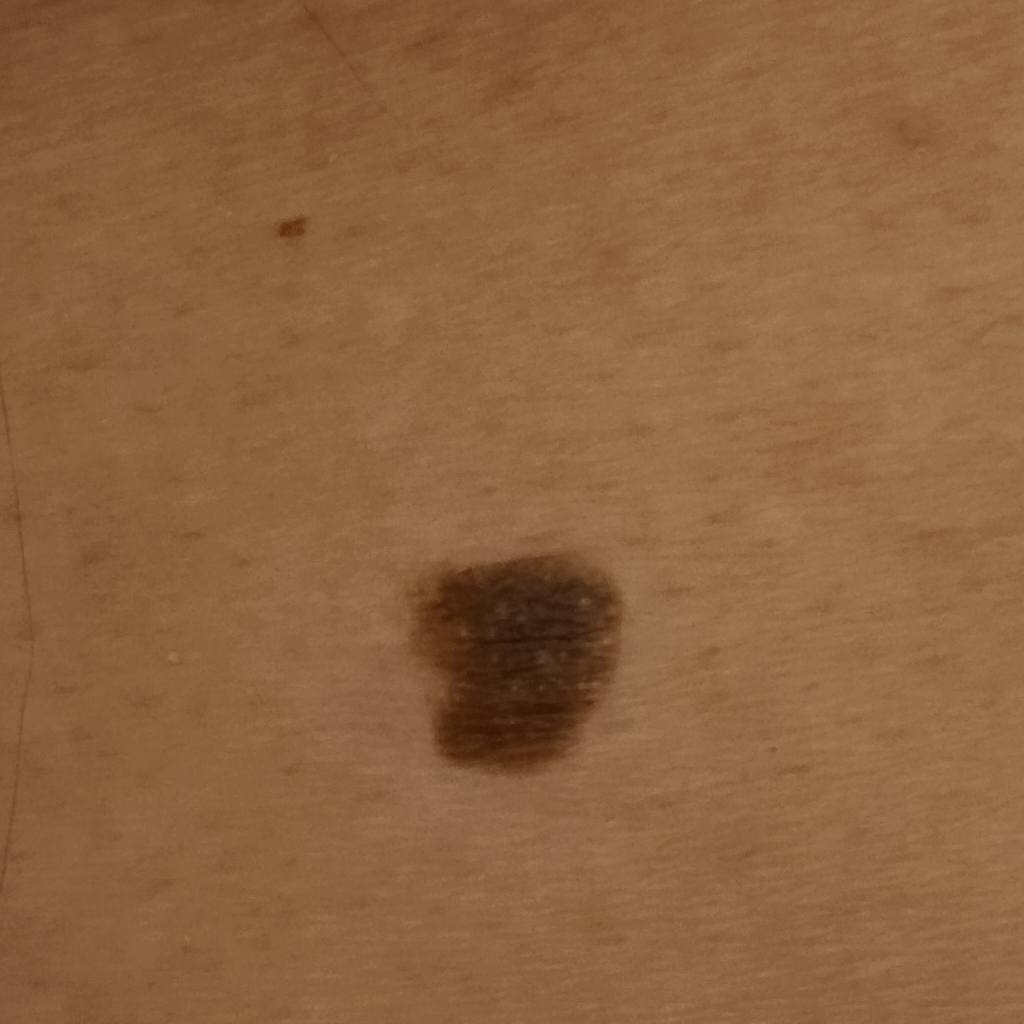A male patient age 76.
A macroscopic clinical photograph of a skin lesion.
Imaged for a research study, with no referral diagnosis recorded.
The lesion measures approximately 8.6 mm.
The consensus diagnosis for this lesion was a seborrheic keratosis.